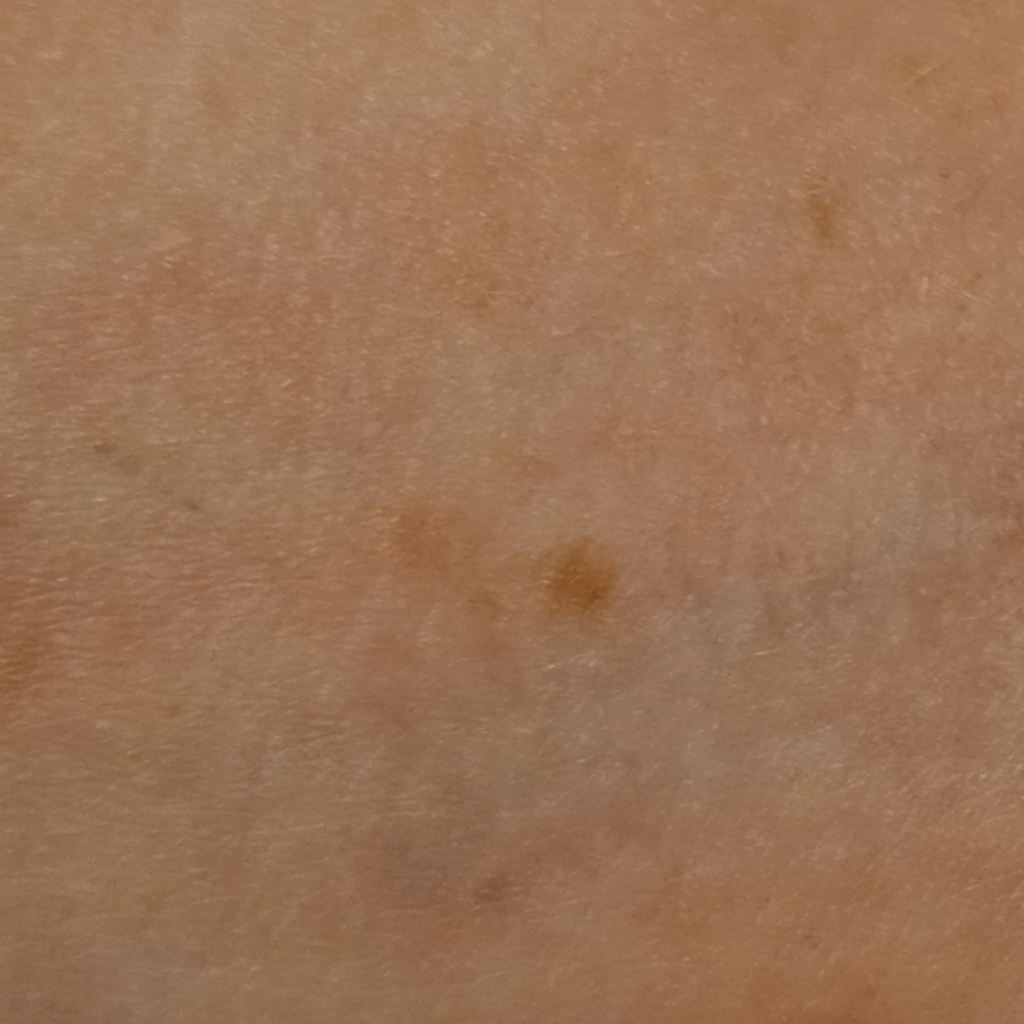subject: female, aged 59; clinical context: research study (no referral diagnosis); nevus count: a moderate number of melanocytic nevi; sun reaction: skin reddens with sun exposure; image type: clinical photo; assessment: melanocytic nevus (dermatologist consensus).